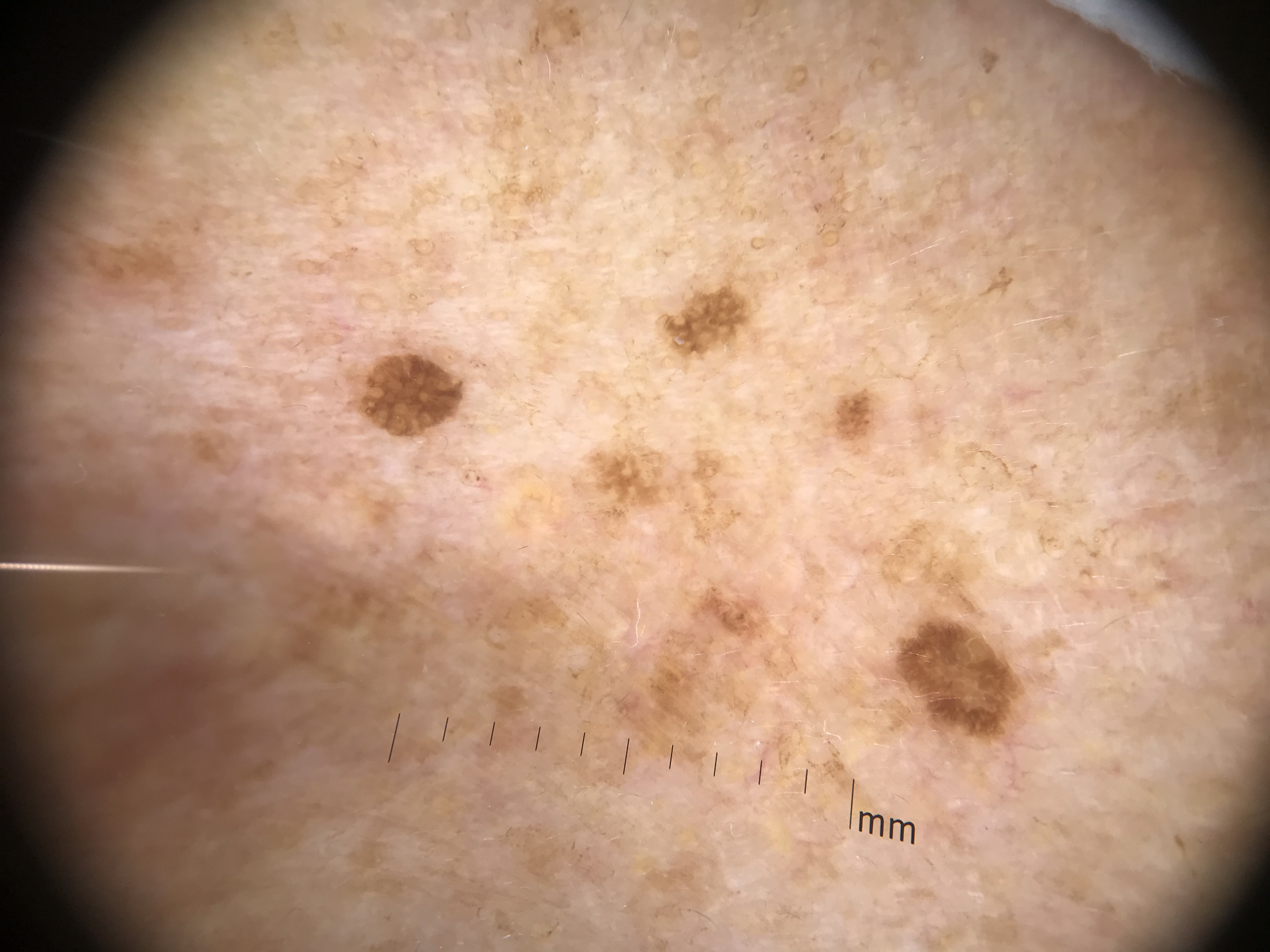Case:
- label · seborrheic keratosis (expert consensus)